A dermoscopic image of a skin lesion:
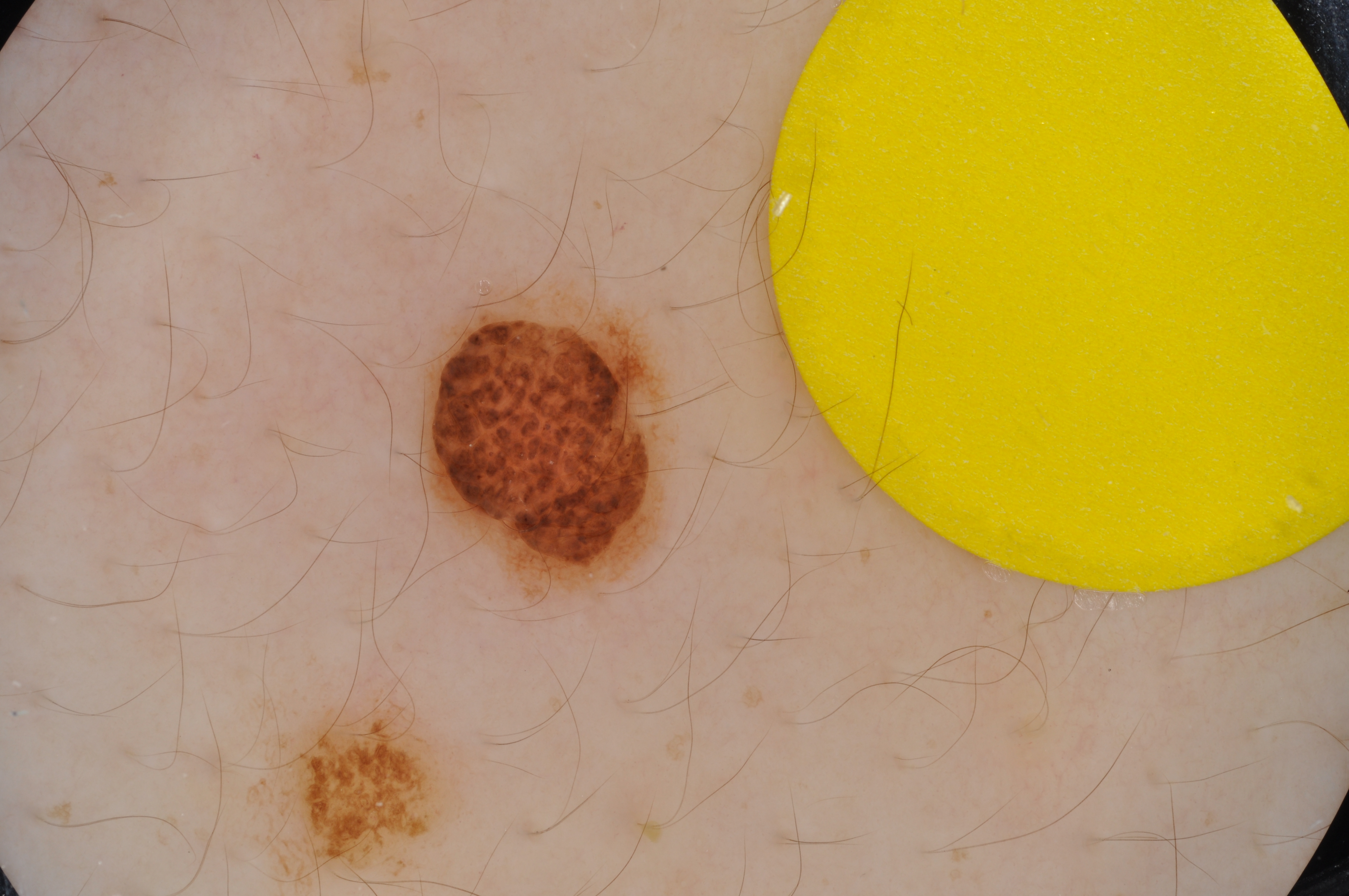{"lesion_location": {"bbox_xyxy": [418, 287, 679, 609]}, "lesion_extent": "small", "diagnosis": {"malignancy": "benign", "provenance": "clinical"}}